A close-up photograph. No constitutional symptoms were reported. The condition has been present for one to three months. Self-categorized by the patient as a rash. The back of the torso, arm and leg are involved — 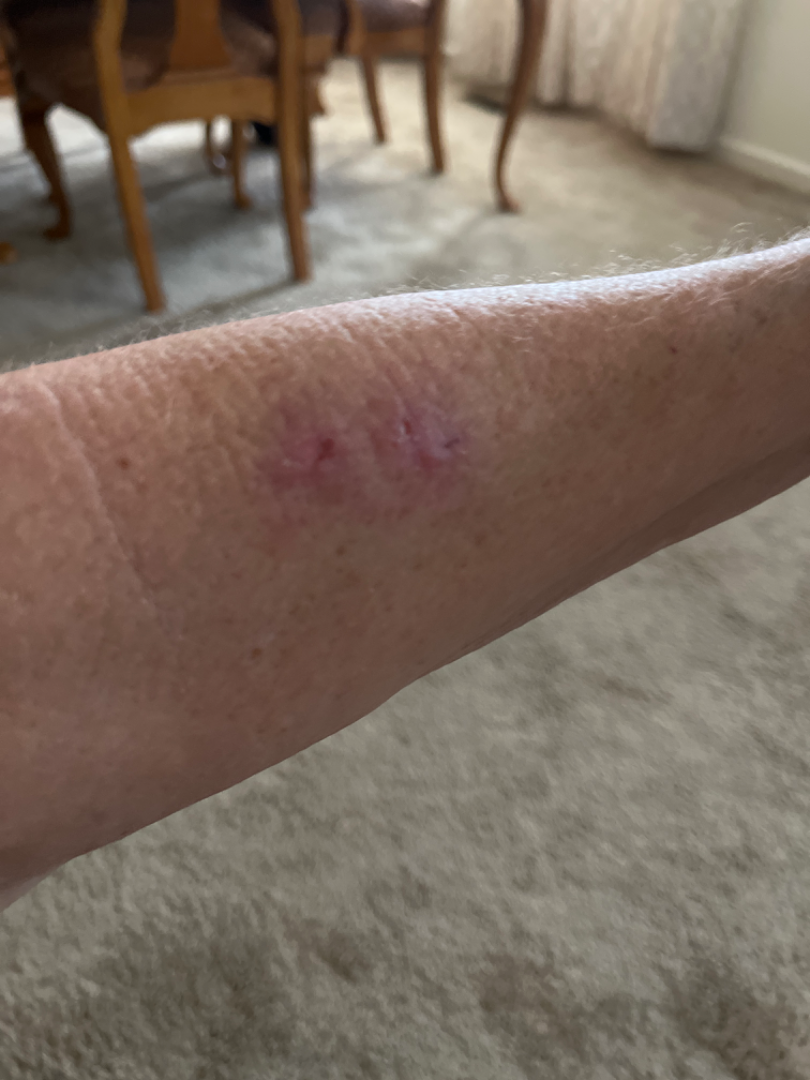One reviewing dermatologist: favoring SCC/SCCIS; also consider Basal Cell Carcinoma.